A dermoscopic close-up of a skin lesion: 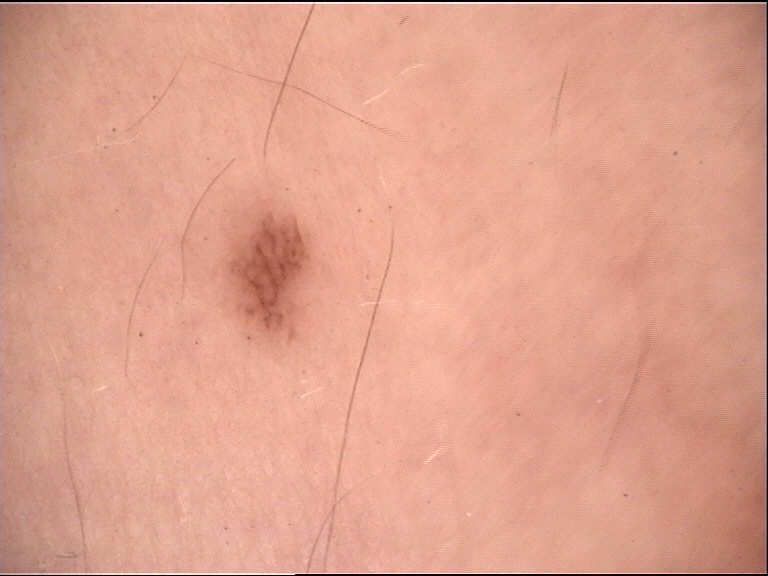diagnostic label = junctional nevus (expert consensus).